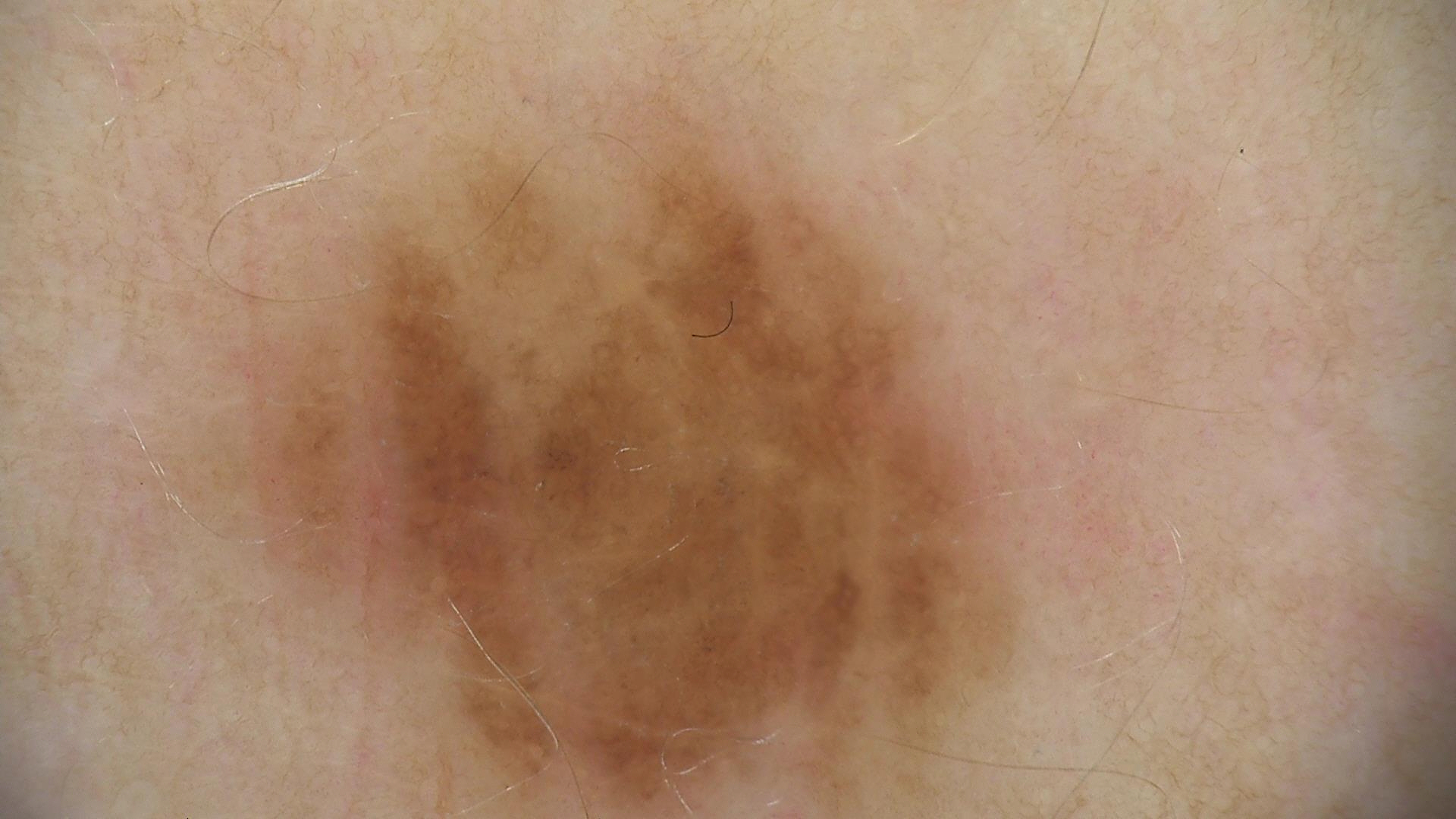A skin lesion imaged with a dermatoscope. Labeled as a benign lesion — a dysplastic junctional nevus.